A skin lesion imaged with a dermatoscope: 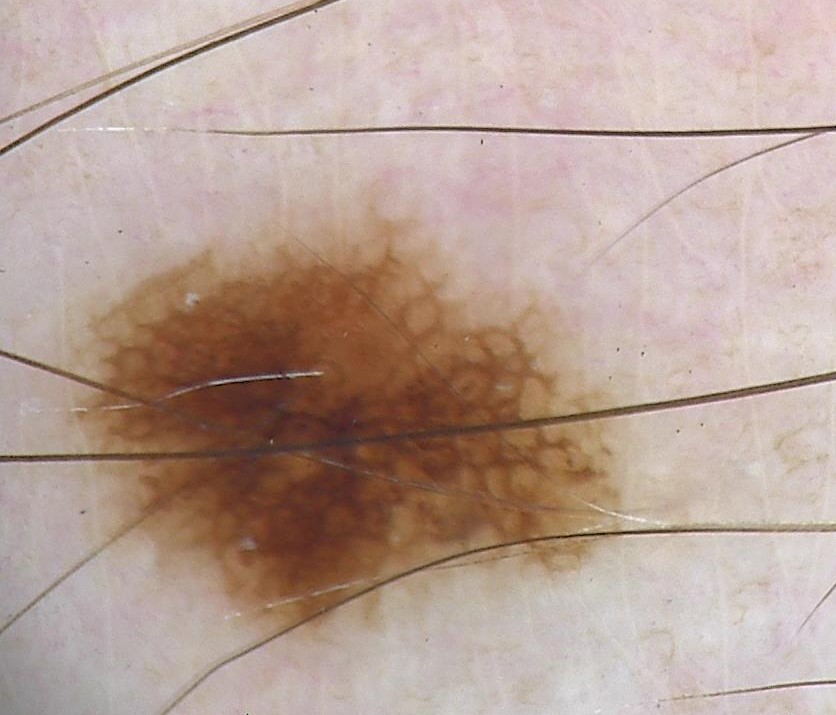Case:
The architecture is that of a banal lesion.
Impression:
Diagnosed as a junctional nevus.